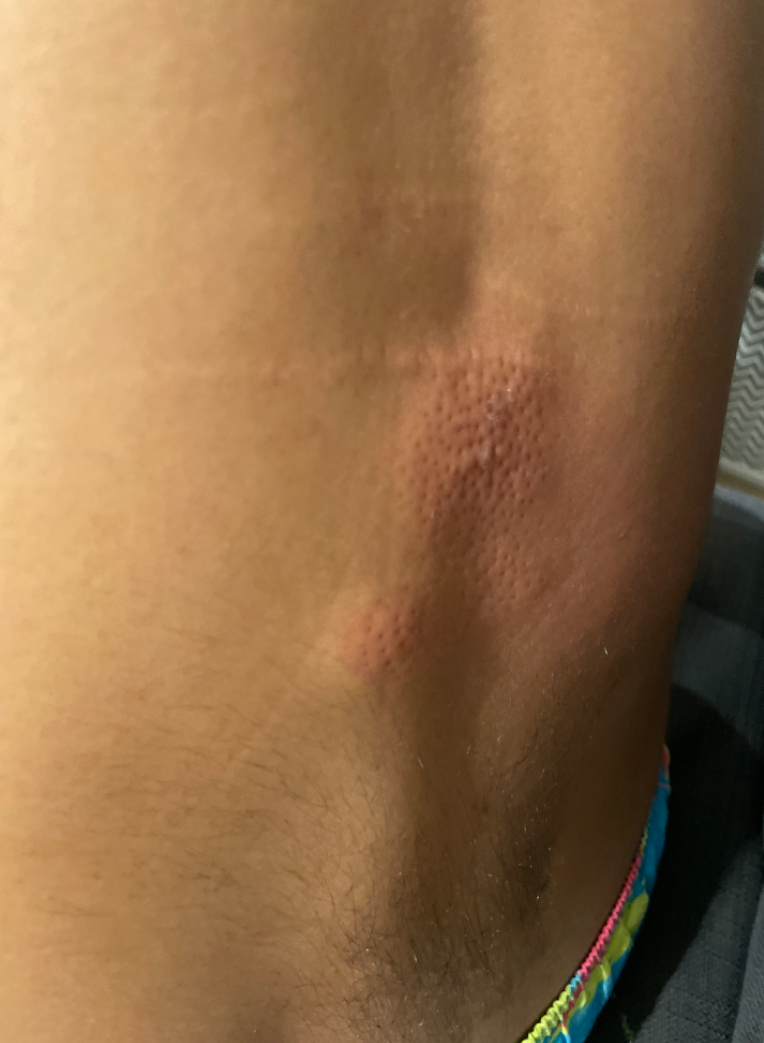Findings: The image was not sufficient for the reviewer to characterize the skin condition.